The photograph was taken at a distance.
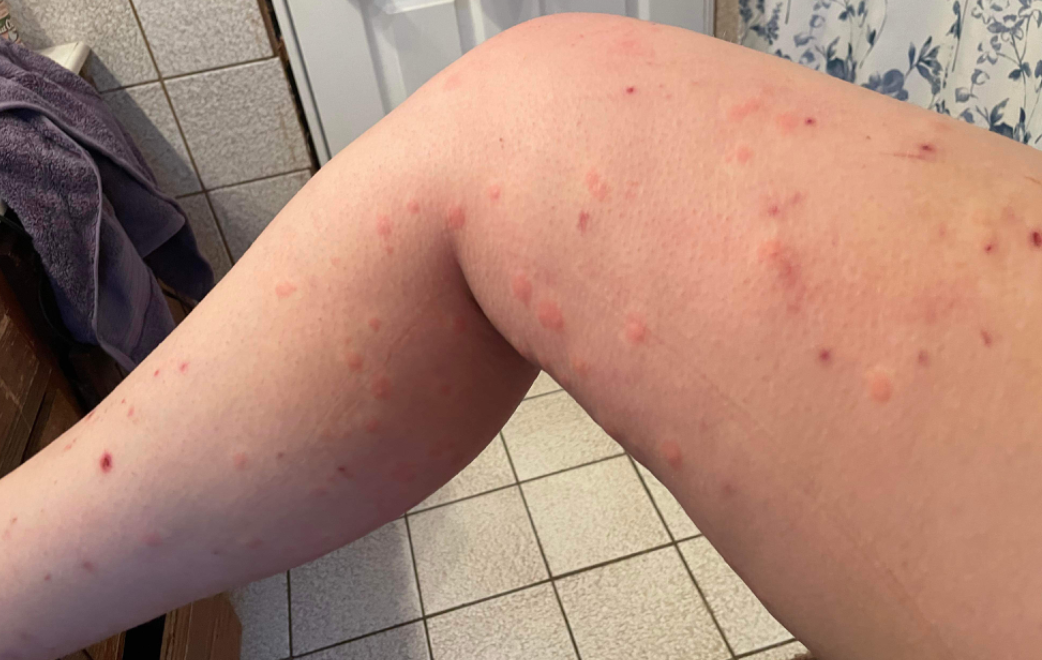Pityriasis lichenoides (possible); Scabies (possible); Insect Bite (possible).